This image was taken at an angle — 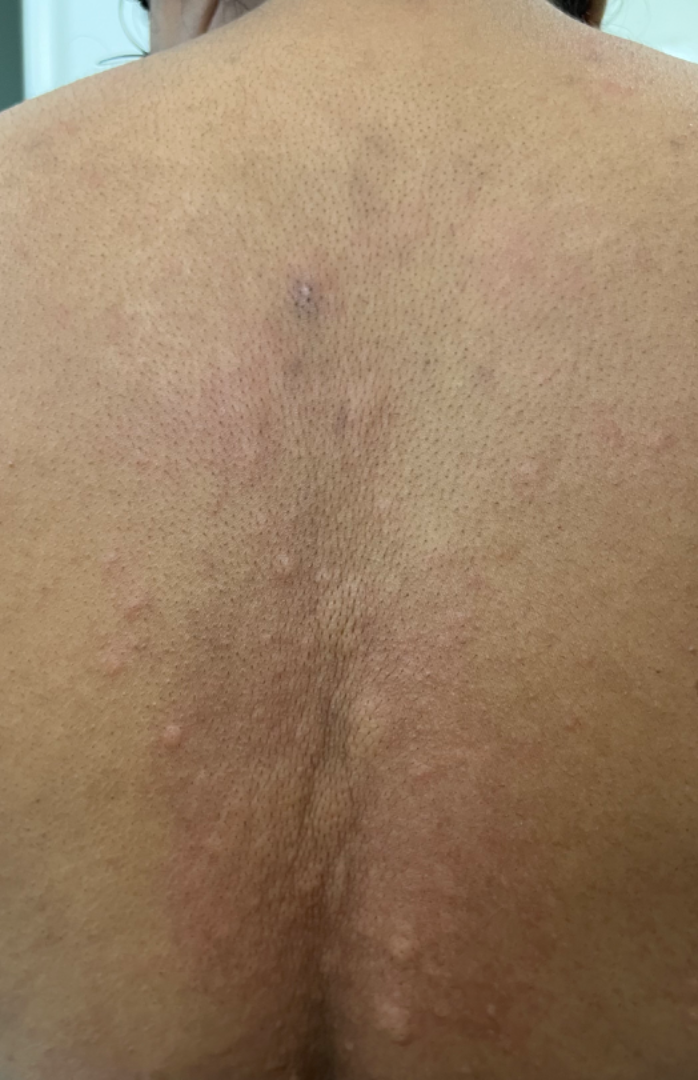| key | value |
|---|---|
| patient's own categorization | acne |
| symptom duration | about one day |
| surface texture | raised or bumpy |
| symptoms | itching |
| impression | Urticaria (0.67); Allergic Contact Dermatitis (0.33) |